No associated systemic symptoms reported · a close-up photograph · the contributor is a female aged 30–39 · the patient indicates the condition has been present for less than one week · located on the head or neck, palm, leg and back of the hand · the patient described the issue as a rash · the patient indicates itching, burning, pain and bothersome appearance.
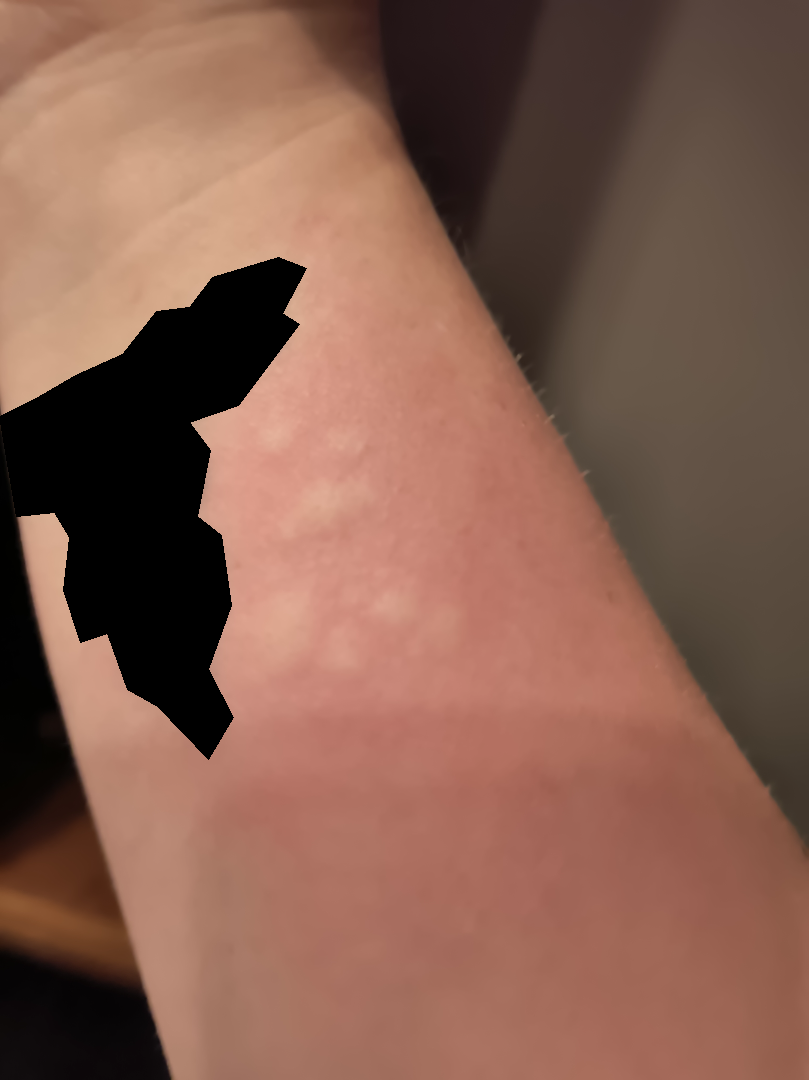differential diagnosis: the leading consideration is Urticaria; possibly Insect Bite; also raised was Allergic Contact Dermatitis